The patient describes having a moderate number of moles; by self-report, a prior organ transplant and immunosuppression; a dermoscopy image of a skin lesion; the patient says their skin reddens painfully with sun exposure; imaged for a research study, with no referral diagnosis recorded:
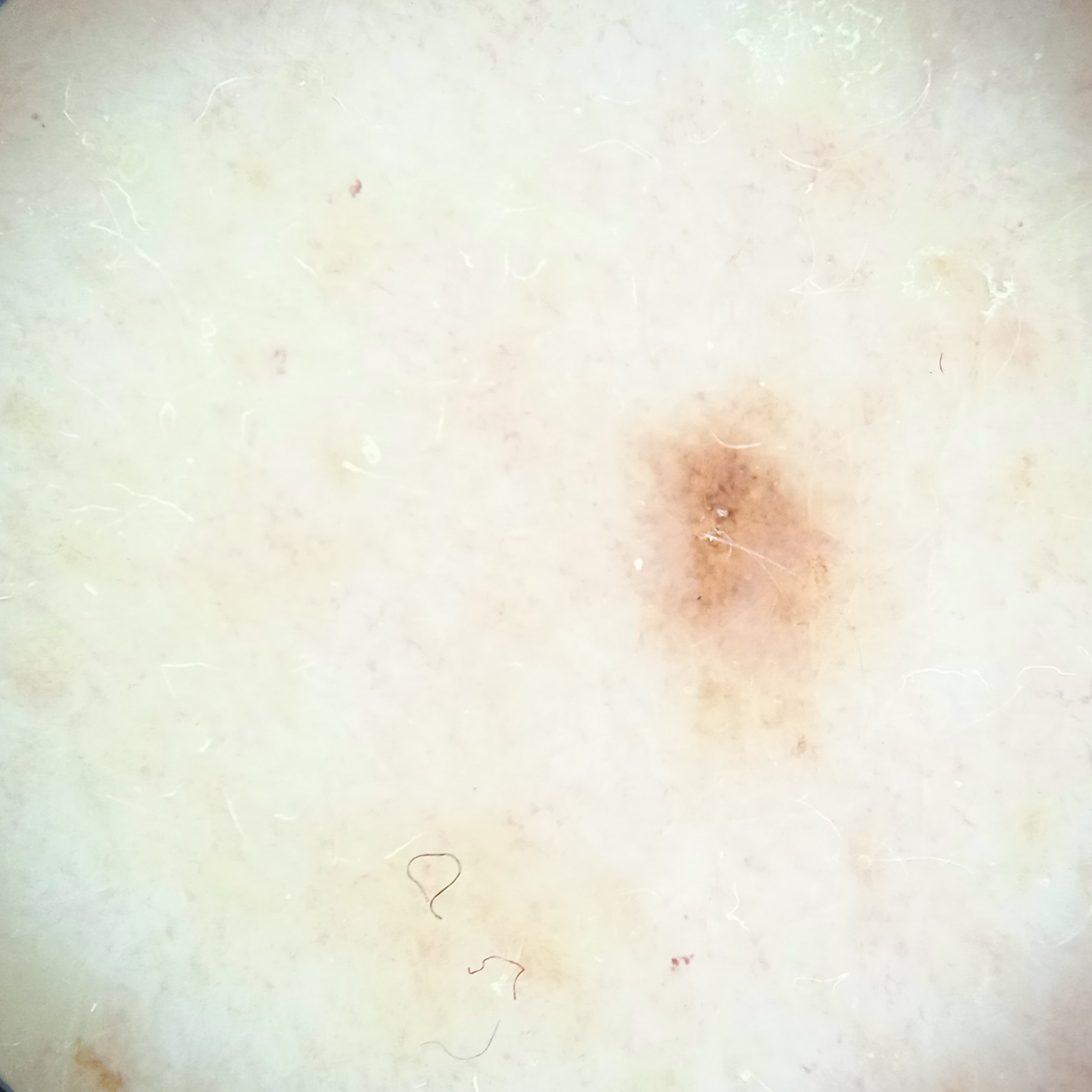{
  "lesion_location": "the back",
  "lesion_size": {
    "diameter_mm": 2.5
  },
  "diagnosis": {
    "name": "melanocytic nevus",
    "malignancy": "benign"
  }
}